The patient is female, the patient considered this a rash, located on the leg and arm, the contributor notes the lesion is flat, this image was taken at an angle, no relevant systemic symptoms, the contributor notes itching:
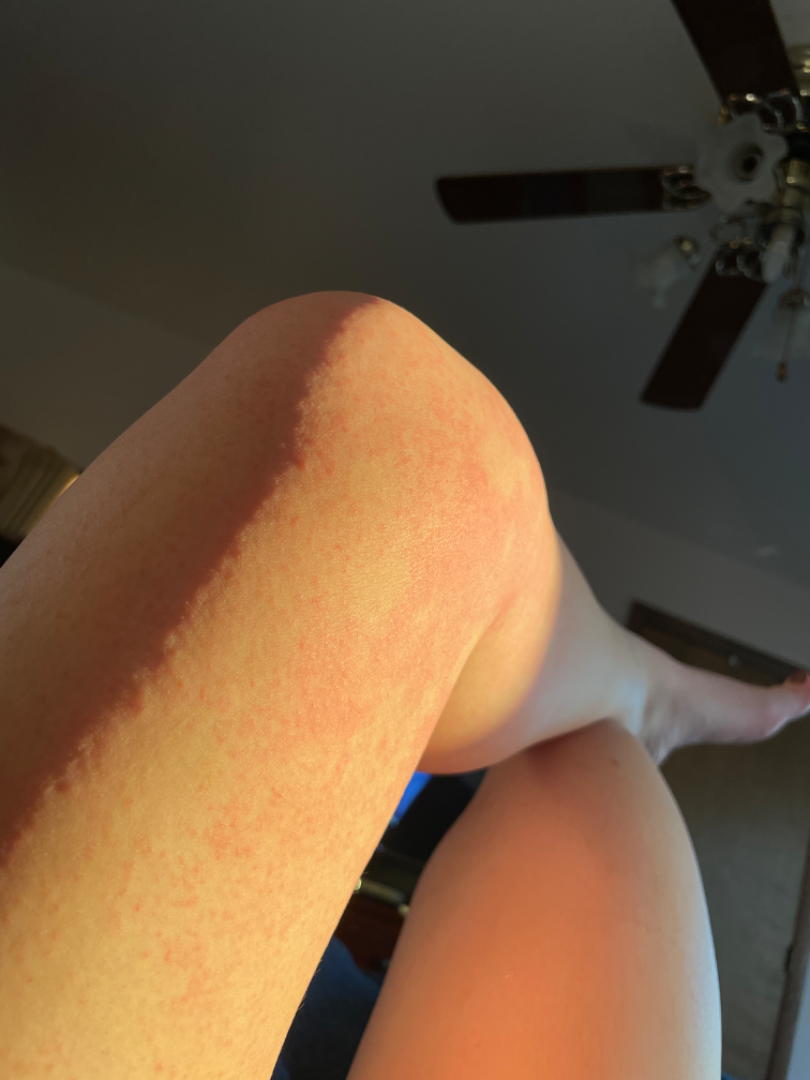{"differential": {"leading": ["Eczema"], "considered": ["Drug Rash", "Urticaria"]}}